A dermatoscopic image of a skin lesion — 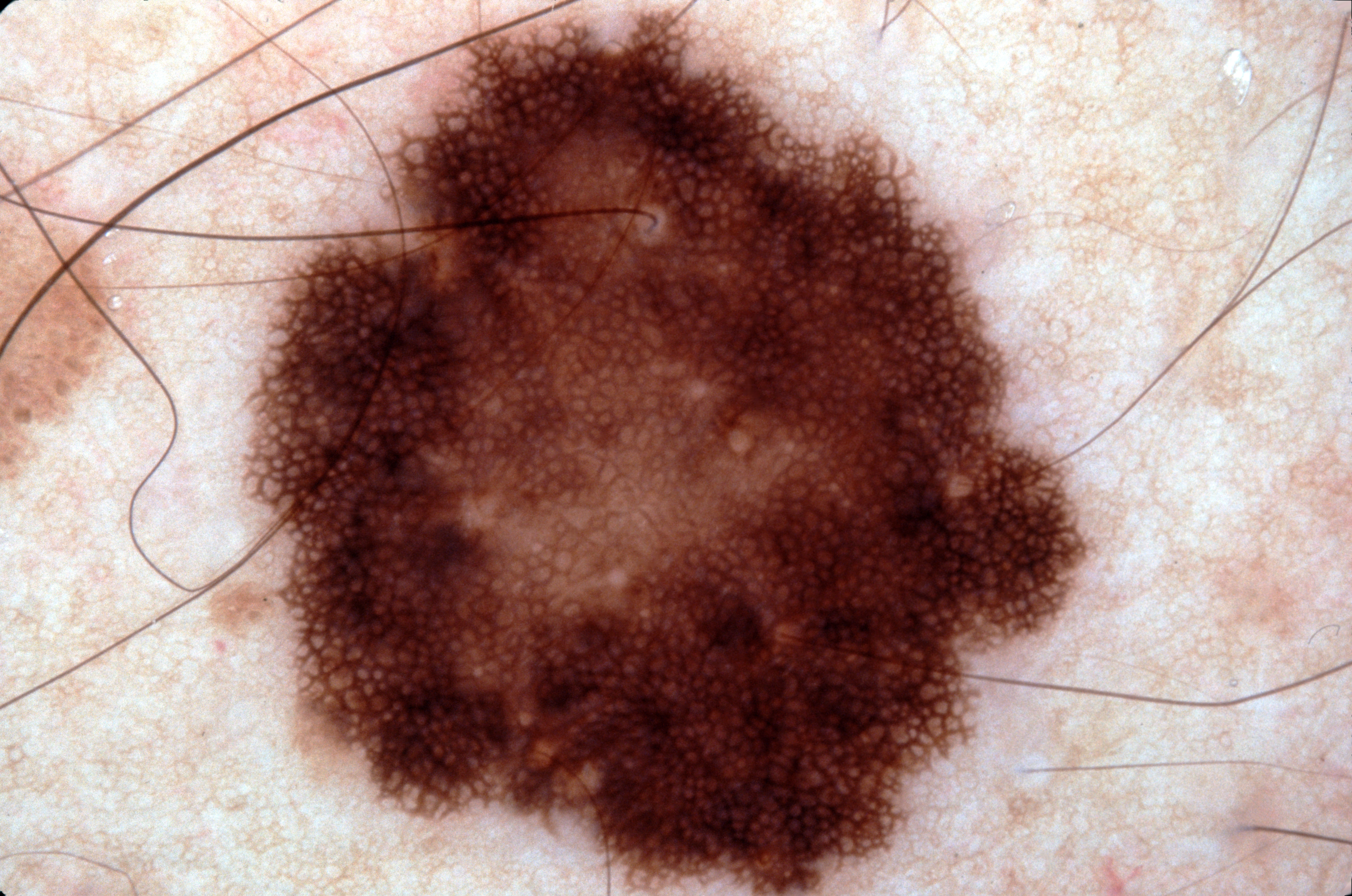{"lesion_location": {"bbox_xyxy": [254, 21, 1088, 895]}, "diagnosis": {"name": "melanocytic nevus", "malignancy": "benign", "lineage": "melanocytic", "provenance": "clinical"}}